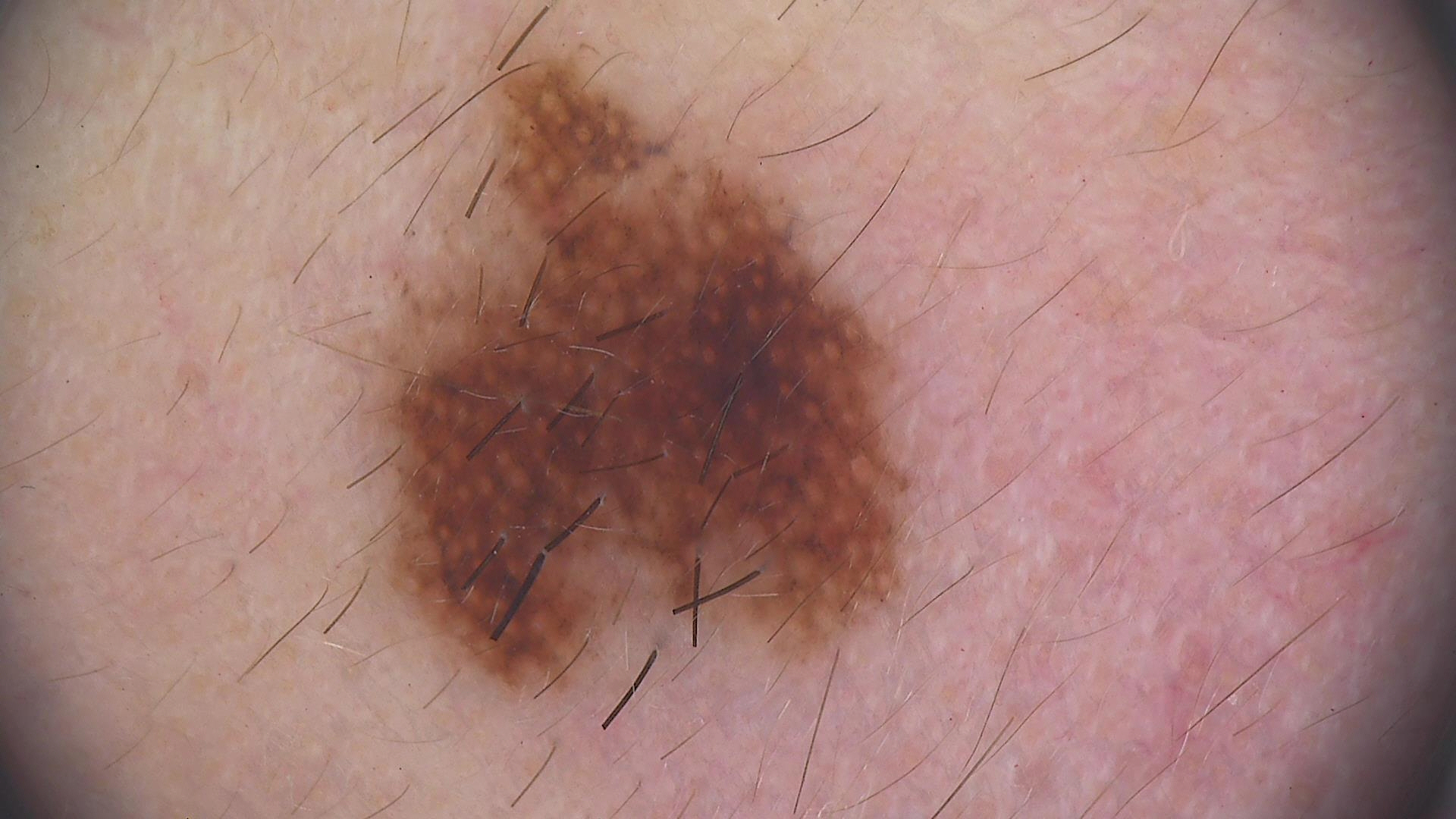Dermoscopy of a skin lesion.
Diagnosed as a dysplastic junctional nevus.